A skin lesion imaged with a dermatoscope: 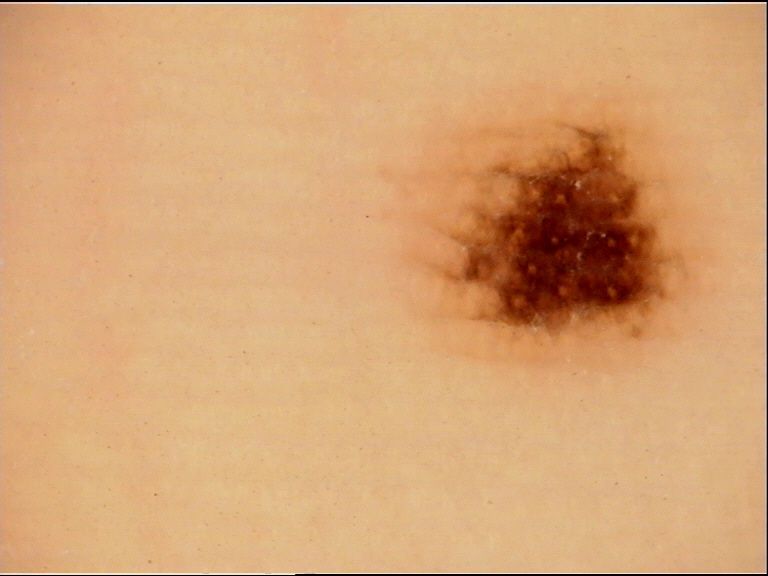Q: What is the diagnosis?
A: acral junctional nevus (expert consensus)